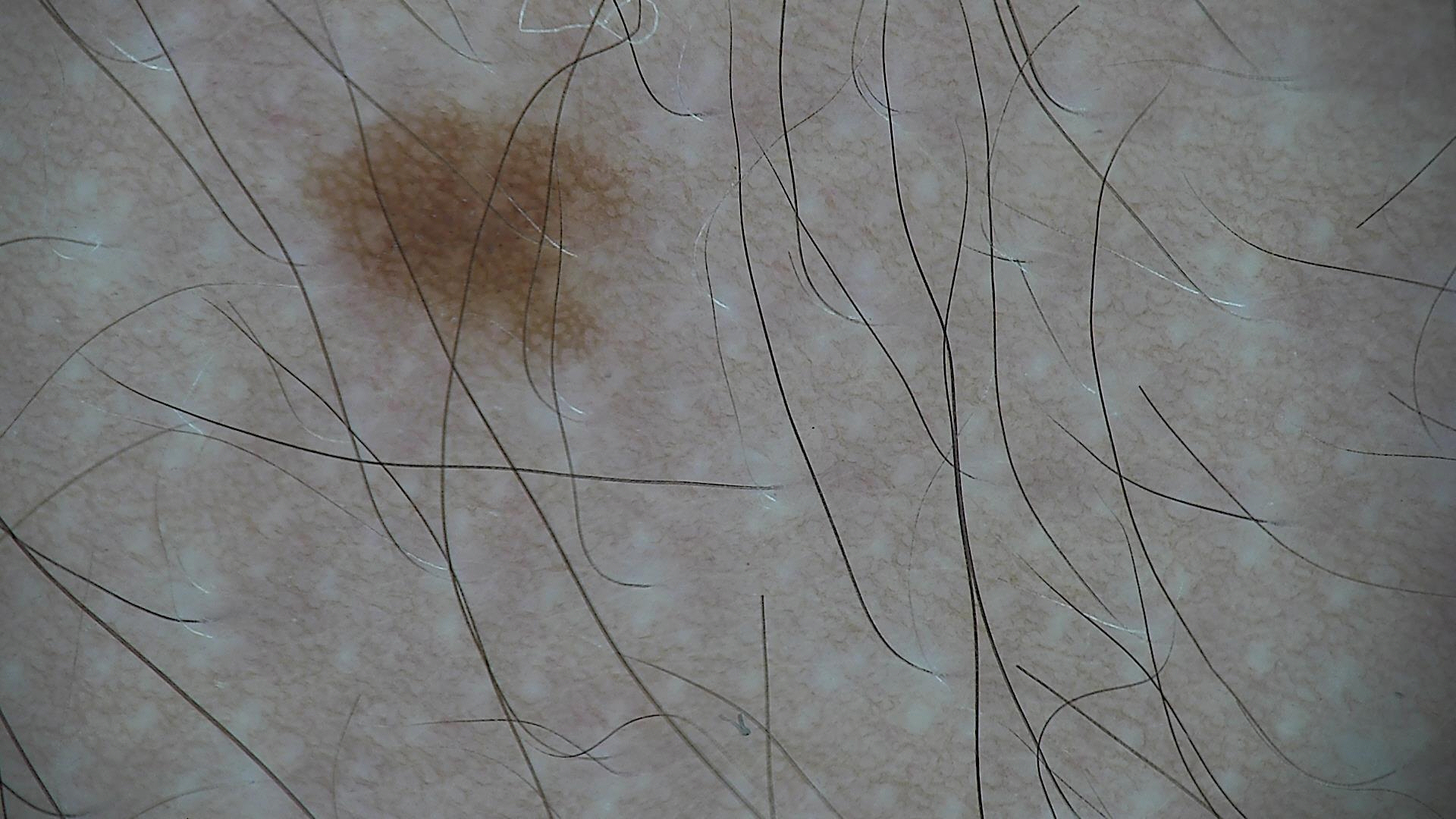| field | value |
|---|---|
| diagnosis | dysplastic junctional nevus (expert consensus) |